The patient describes having a moderate number of moles; a female patient aged 50; referred with a clinical suspicion of melanoma; a skin lesion imaged with a dermatoscope; on a questionnaire the patient reported a personal history of skin cancer, no personal history of cancer, and no prior organ transplant: 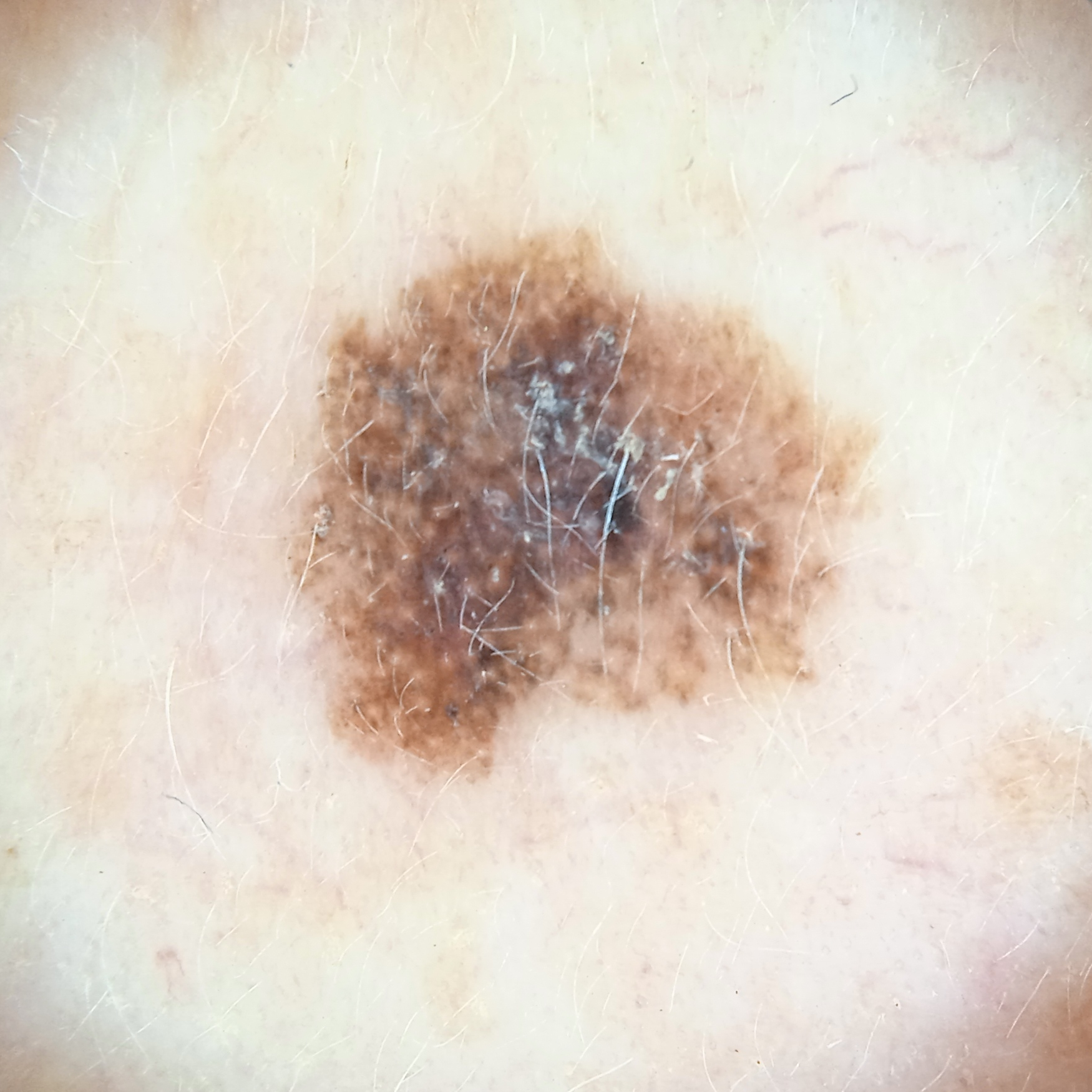Q: What is the anatomic site?
A: the face
Q: Lesion size?
A: 7 mm
Q: What did the biopsy show?
A: melanoma (biopsy-proven)